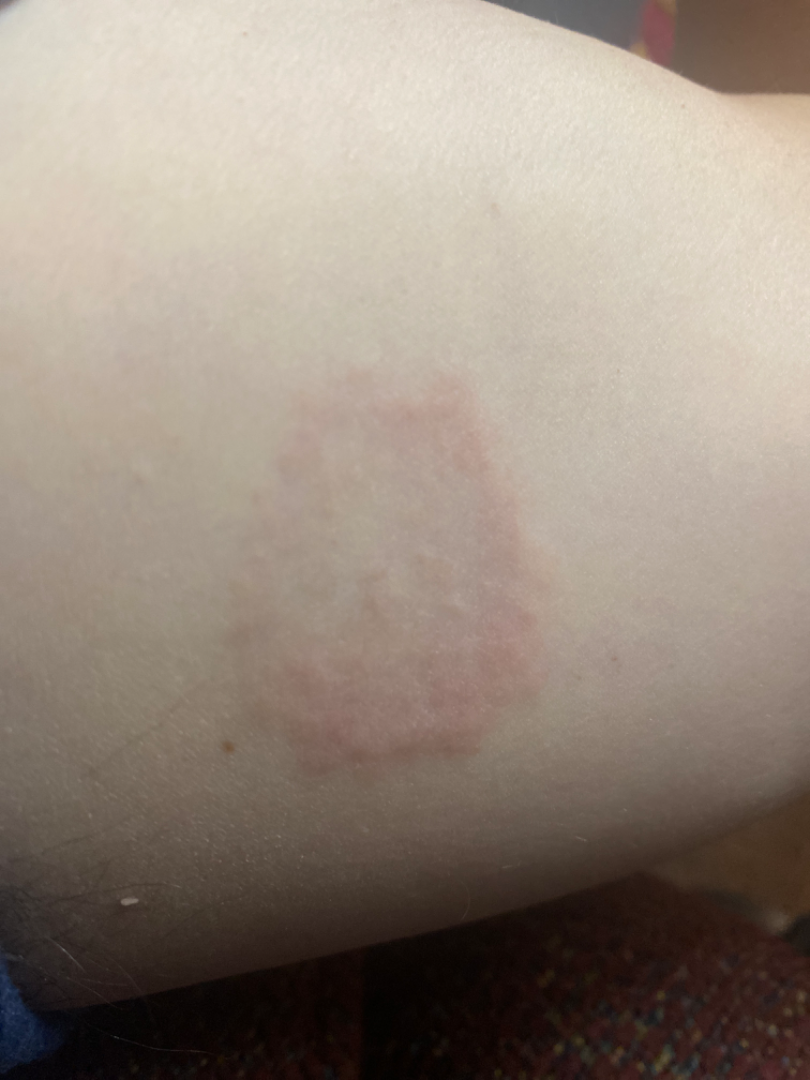Review: The skin findings could not be characterized from the image. Patient information: Human graders estimated Monk Skin Tone 3 (US pool) or 1 (India pool). The subject is a male aged 30–39. Close-up view. The lesion involves the arm. Reported duration is one to three months. Reported lesion symptoms include enlargement. Self-categorized by the patient as a rash. The contributor reports the lesion is raised or bumpy.